A dermoscopy image of a single skin lesion.
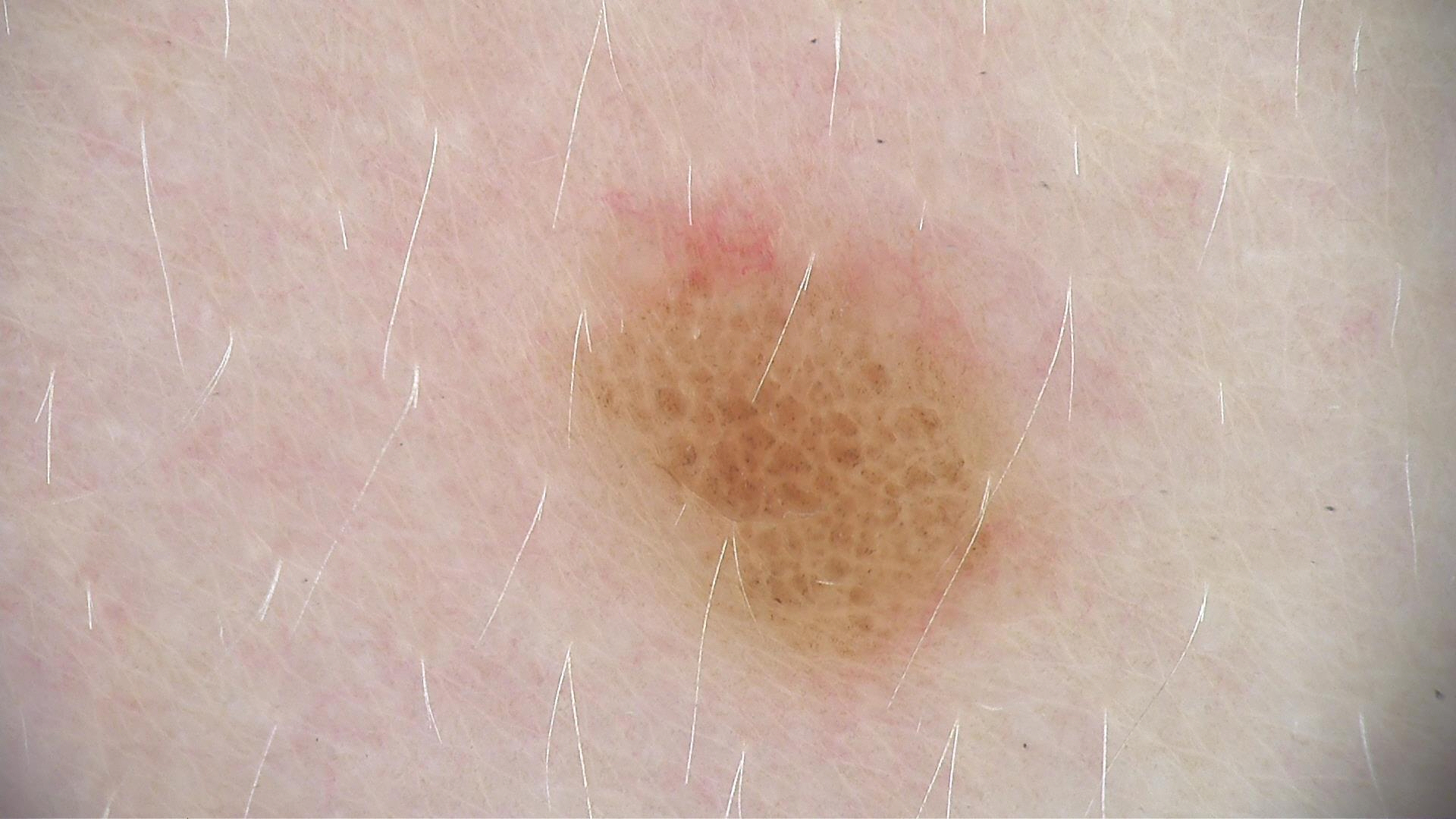Impression:
Consistent with a banal lesion — a compound nevus.